A clinical close-up photograph of a skin lesion. A patient 62 years of age.
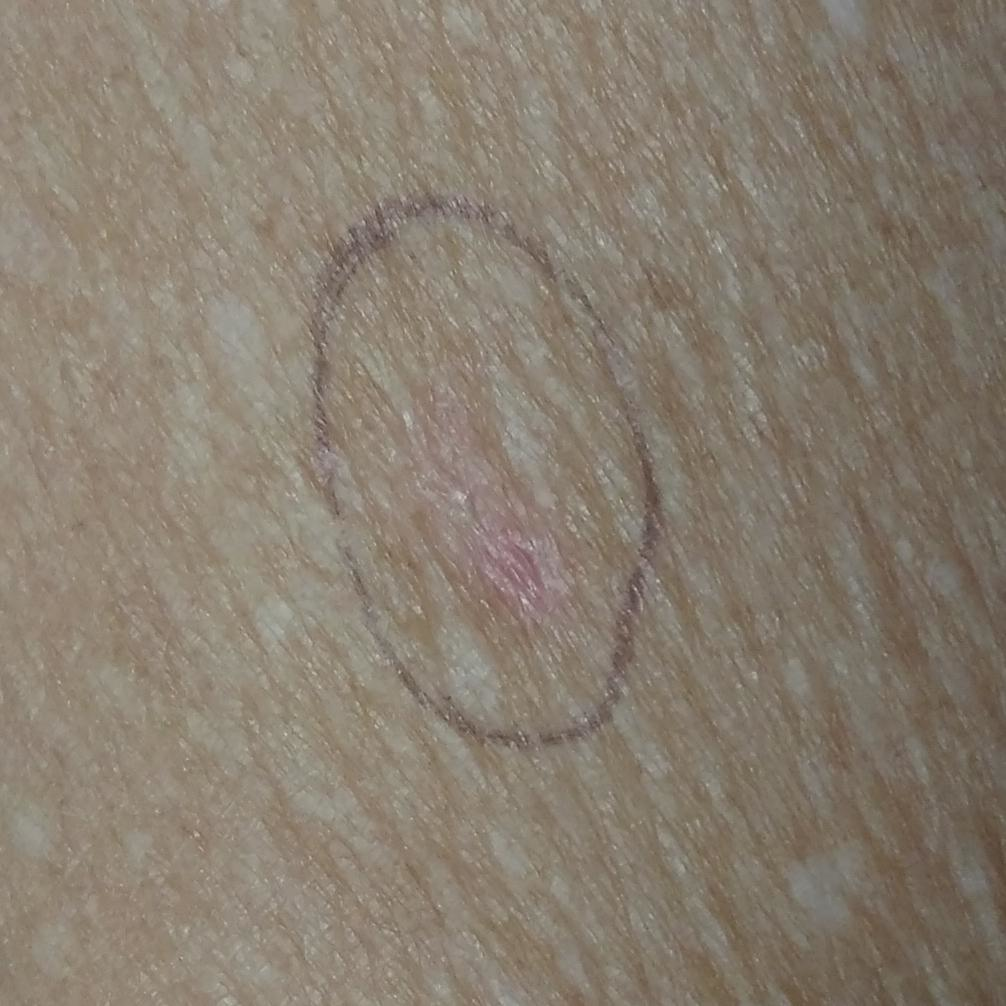<lesion>
  <lesion_location>an arm</lesion_location>
  <diagnosis>
    <name>actinic keratosis</name>
    <code>ACK</code>
    <malignancy>indeterminate</malignancy>
    <confirmation>clinical consensus</confirmation>
  </diagnosis>
</lesion>